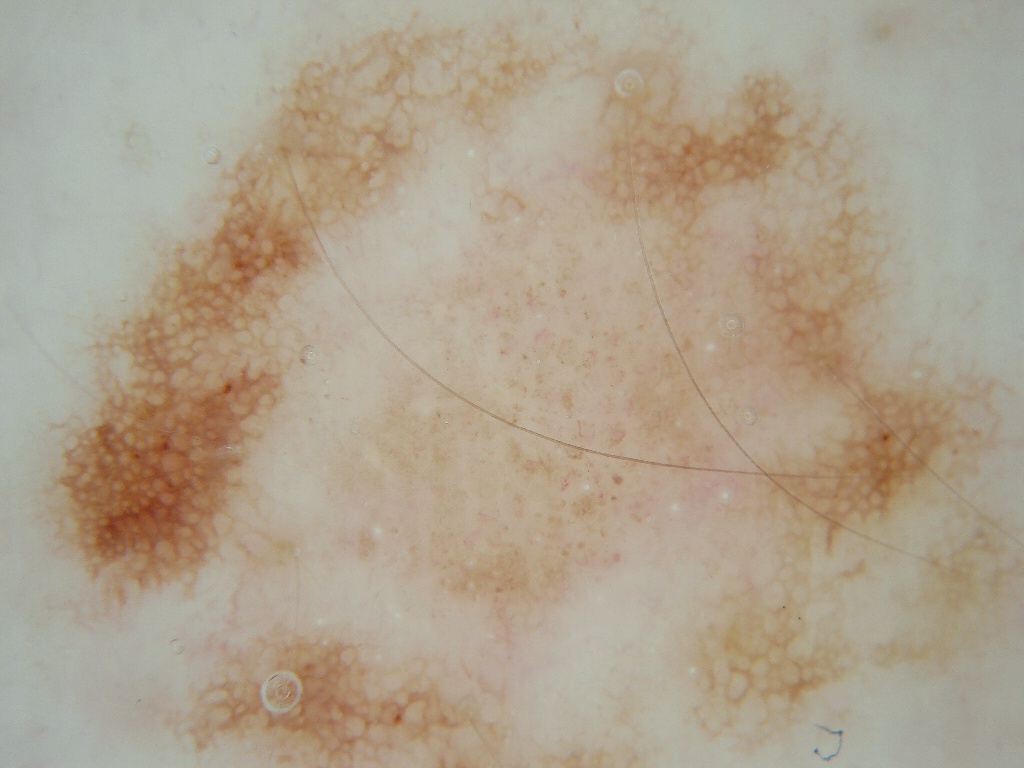Summary: Dermoscopy of a skin lesion. The lesion extends across the full dermoscopic field. Conclusion: Diagnosed as a benign lesion.